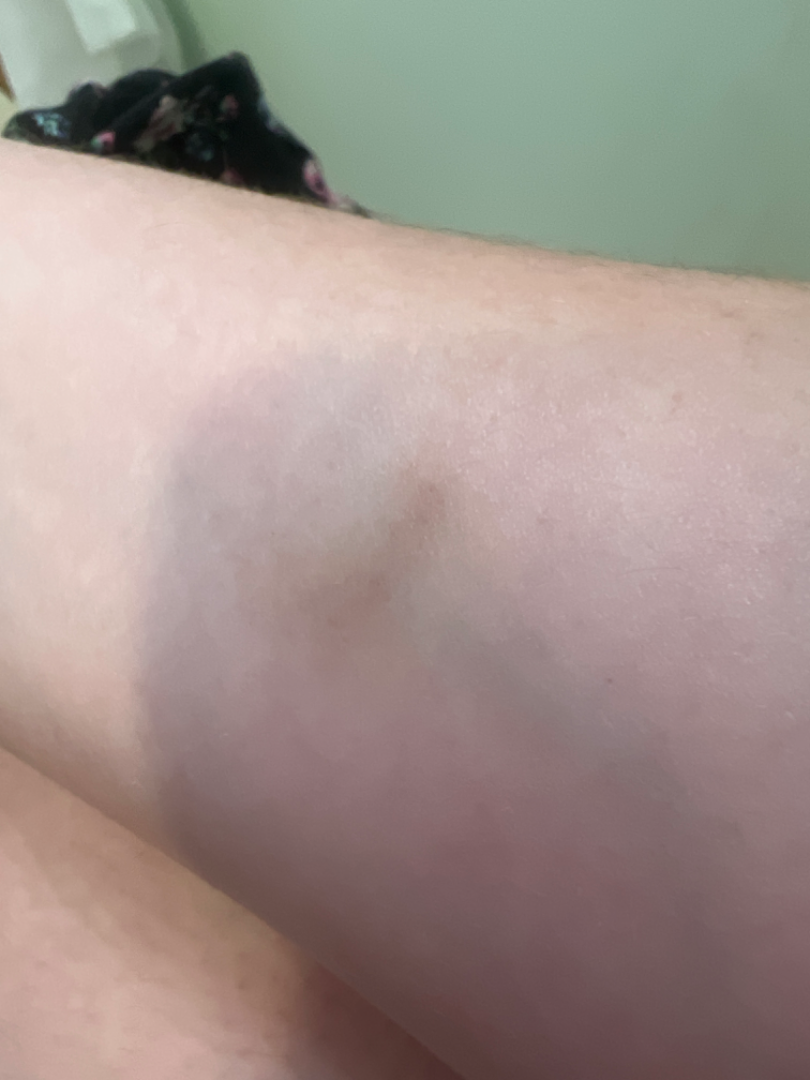  assessment: could not be assessed
  body_site: arm
  shot_type: close-up